A dermoscopic photograph of a skin lesion.
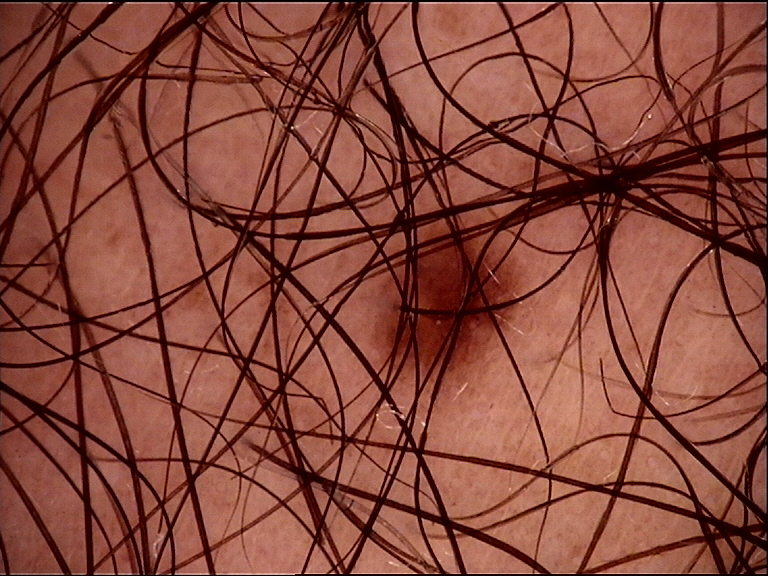Impression: Consistent with a dysplastic junctional nevus.